Present for three to twelve months; this image was taken at an angle; the lesion involves the leg; the patient reports bothersome appearance; the patient considered this a pigmentary problem; the subject is a female aged 30–39; the lesion is described as rough or flaky and flat: 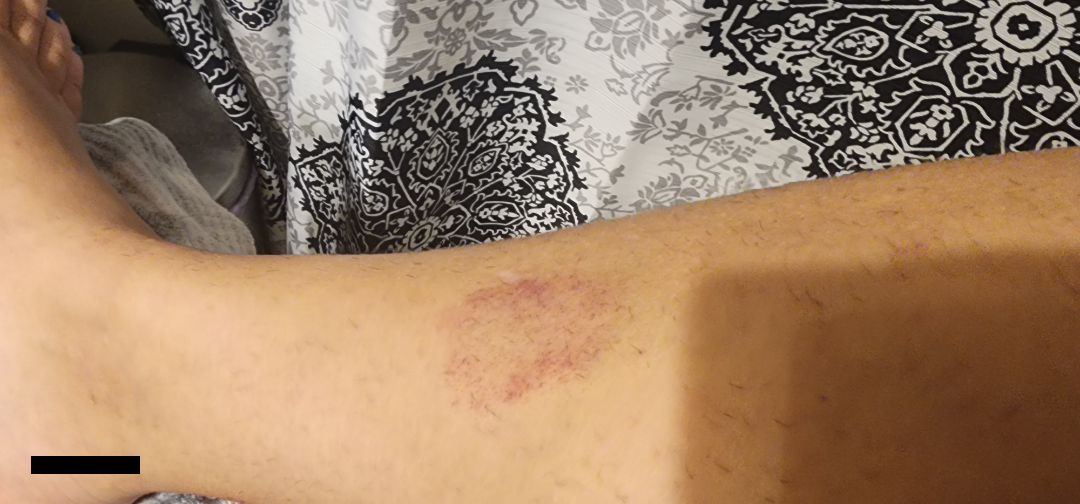On photographic review by a dermatologist: the primary impression is Purpura; the differential also includes Hemangioma; possibly Drug Rash.